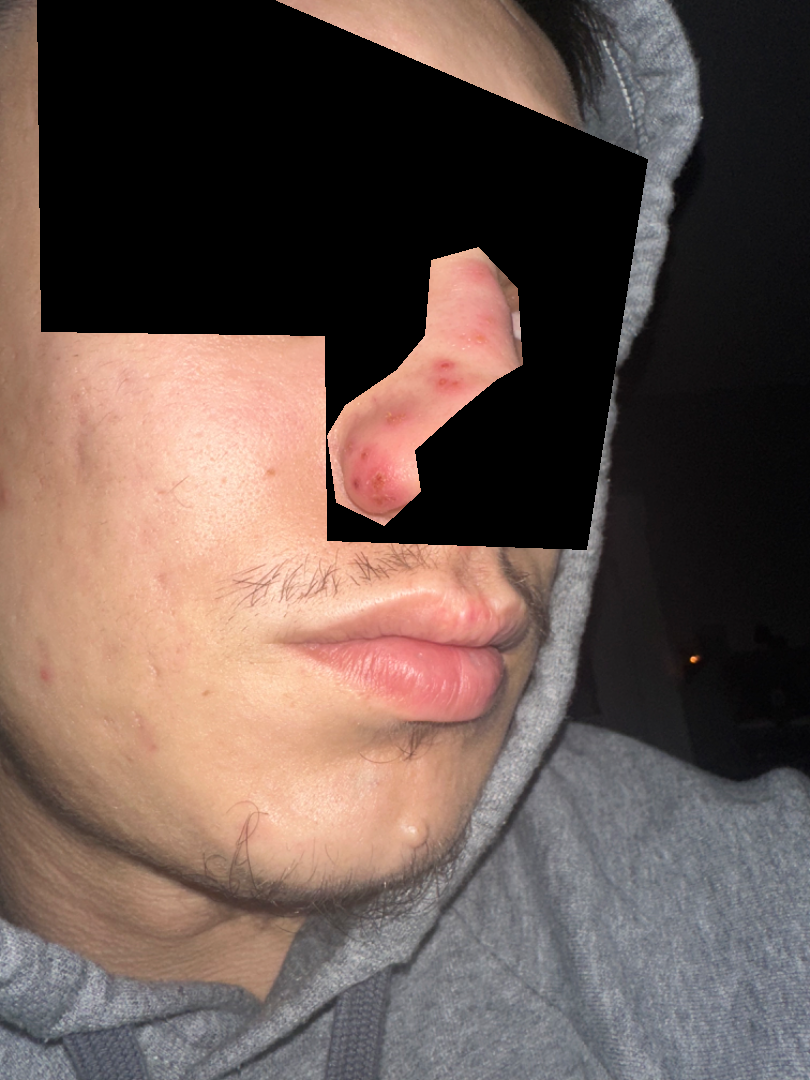Patient information:
The patient indicates the condition has been present for less than one week. No associated systemic symptoms reported. The subject is 18–29, male. An image taken at a distance. Symptoms reported: pain and itching. The patient indicates the lesion is rough or flaky and fluid-filled.